The photograph was taken at an angle; reported duration is less than one week; the back of the hand is involved.
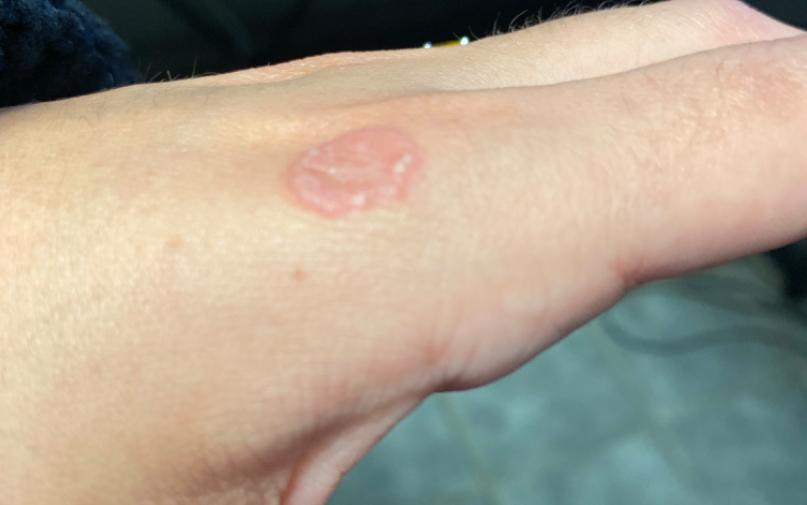{
  "differential": {
    "leading": [
      "Verruca vulgaris"
    ],
    "considered": [
      "Granuloma annulare",
      "Lichen planus/lichenoid eruption"
    ]
  }
}